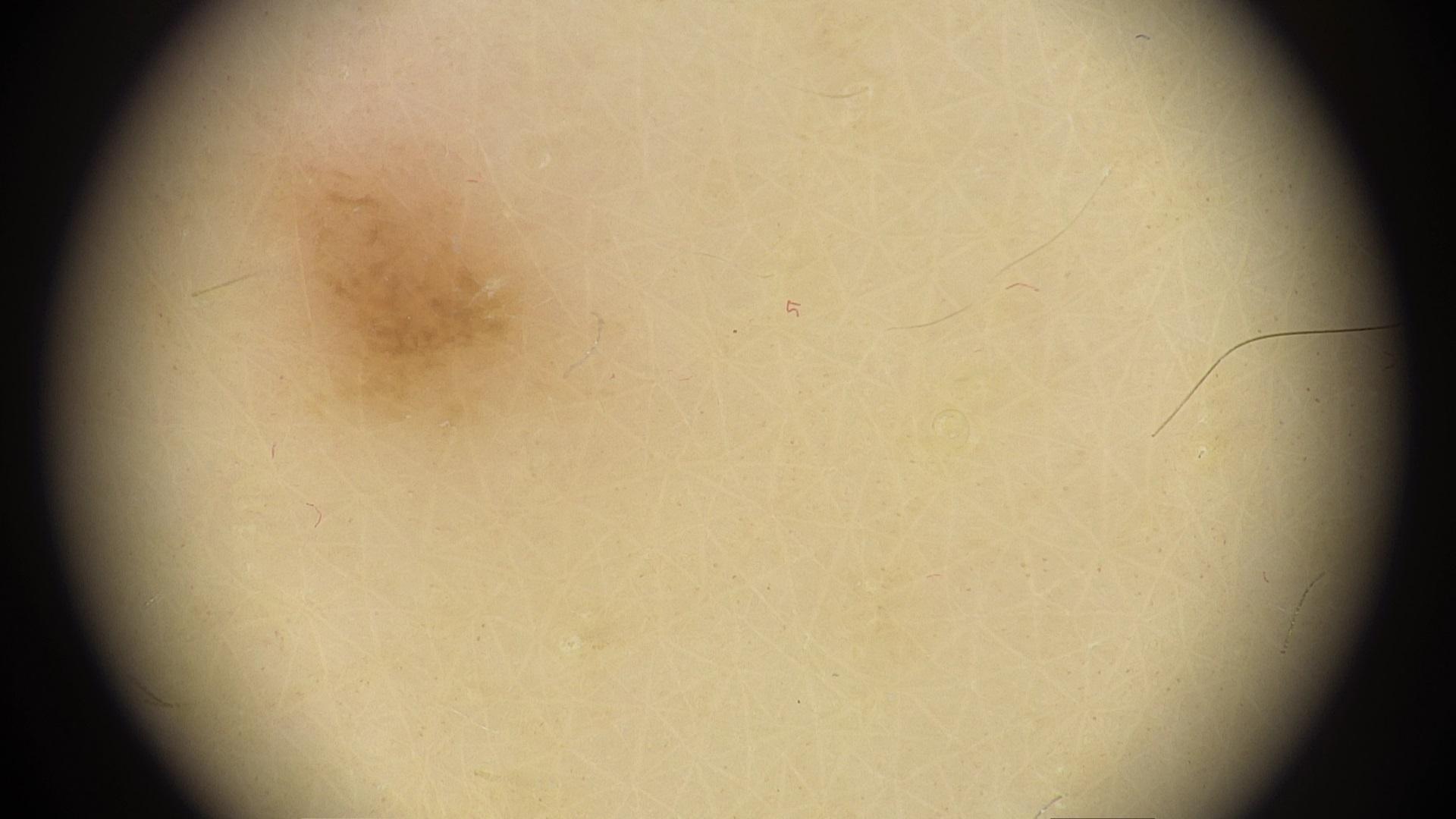{
  "melanoma_history": {
    "personal_hx_melanoma": false,
    "family_hx_melanoma": false
  },
  "skin_type": "II",
  "patient": {
    "age_approx": 35,
    "sex": "female"
  },
  "image": "contact-polarized dermoscopy",
  "lesion_location": {
    "region": "a lower extremity"
  },
  "diagnosis": {
    "name": "Nevus",
    "malignancy": "benign",
    "confirmation": "expert clinical impression",
    "lineage": "melanocytic"
  }
}